Dermoscopy of a skin lesion.
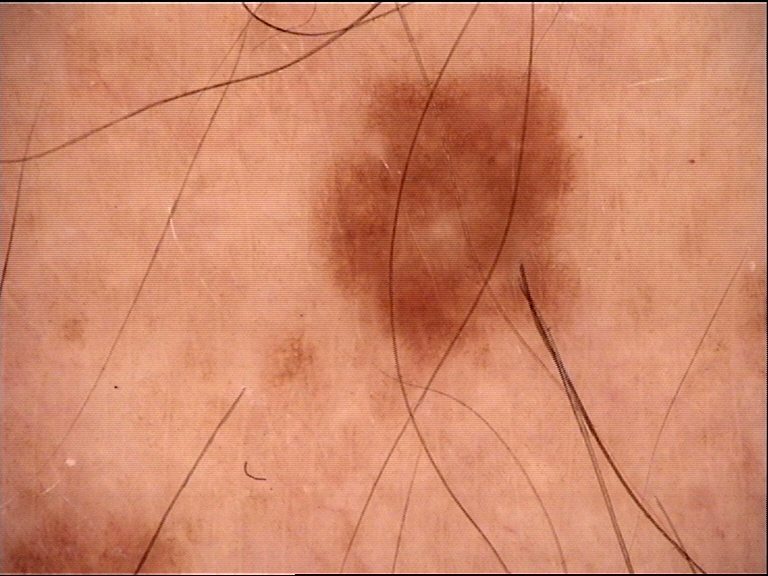Labeled as a dysplastic junctional nevus.